The photograph was taken at a distance:
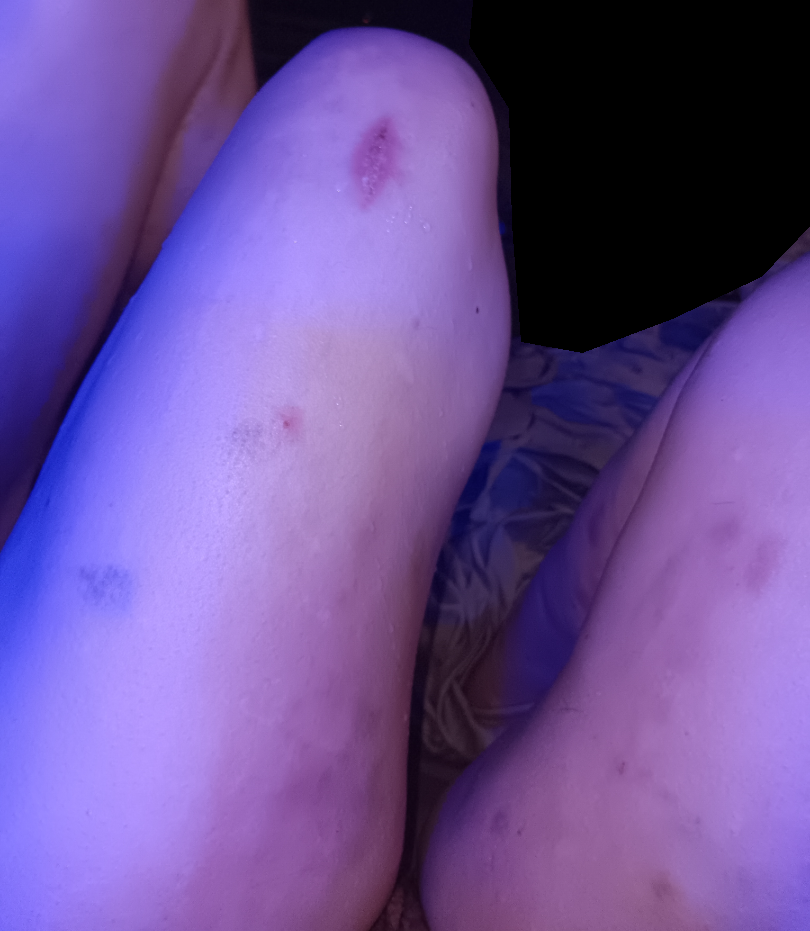differential:
  leading:
    - Allergic Contact Dermatitis